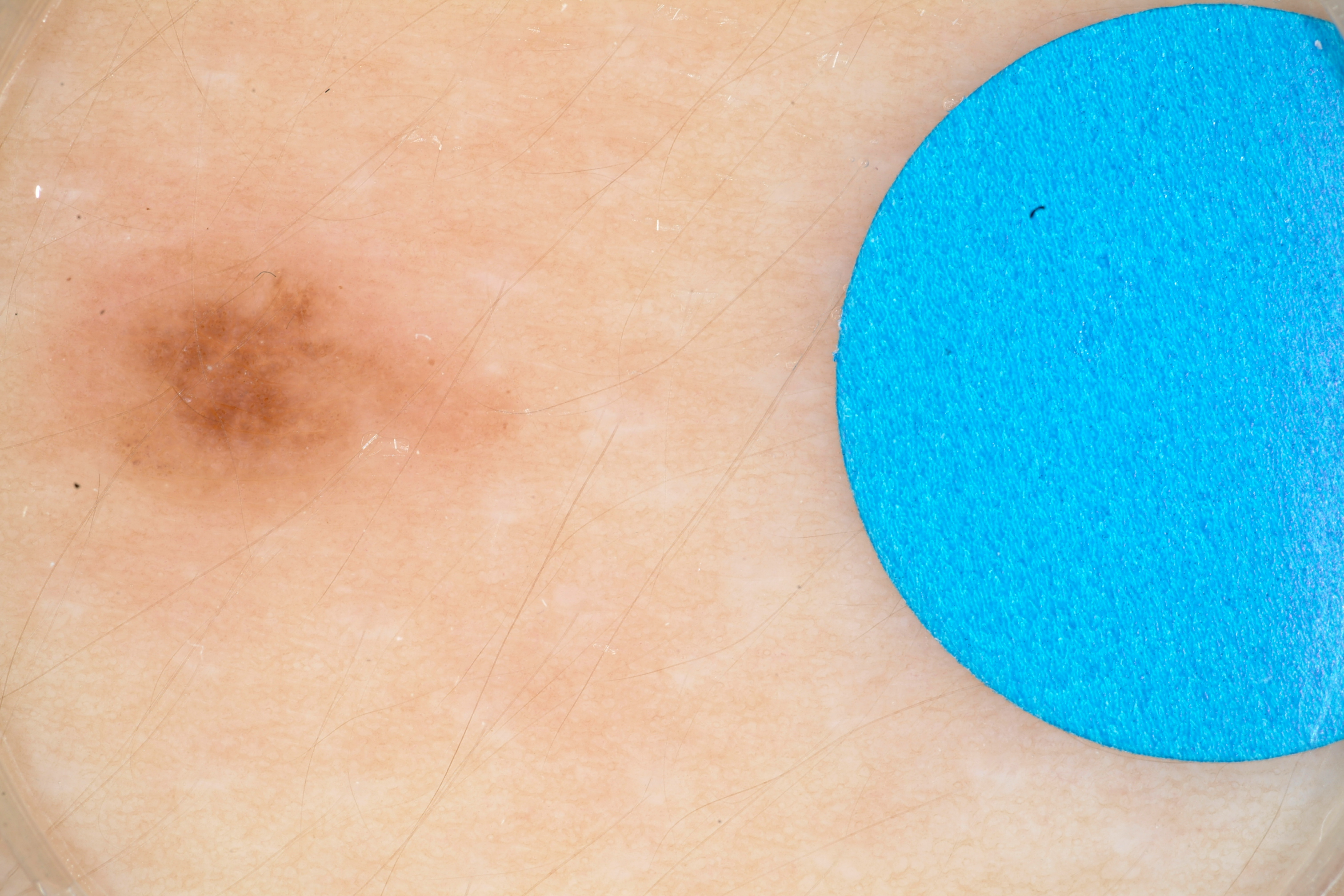Summary: A dermoscopic close-up of a skin lesion. The patient is a female aged 13-17. In (x1, y1, x2, y2) order, the lesion's extent is [45,230,535,523]. The lesion occupies roughly 8% of the field. Dermoscopy demonstrates milia-like cysts and globules, with no pigment network, negative network, or streaks. Conclusion: Expert review diagnosed this as a melanocytic nevus, a benign lesion.